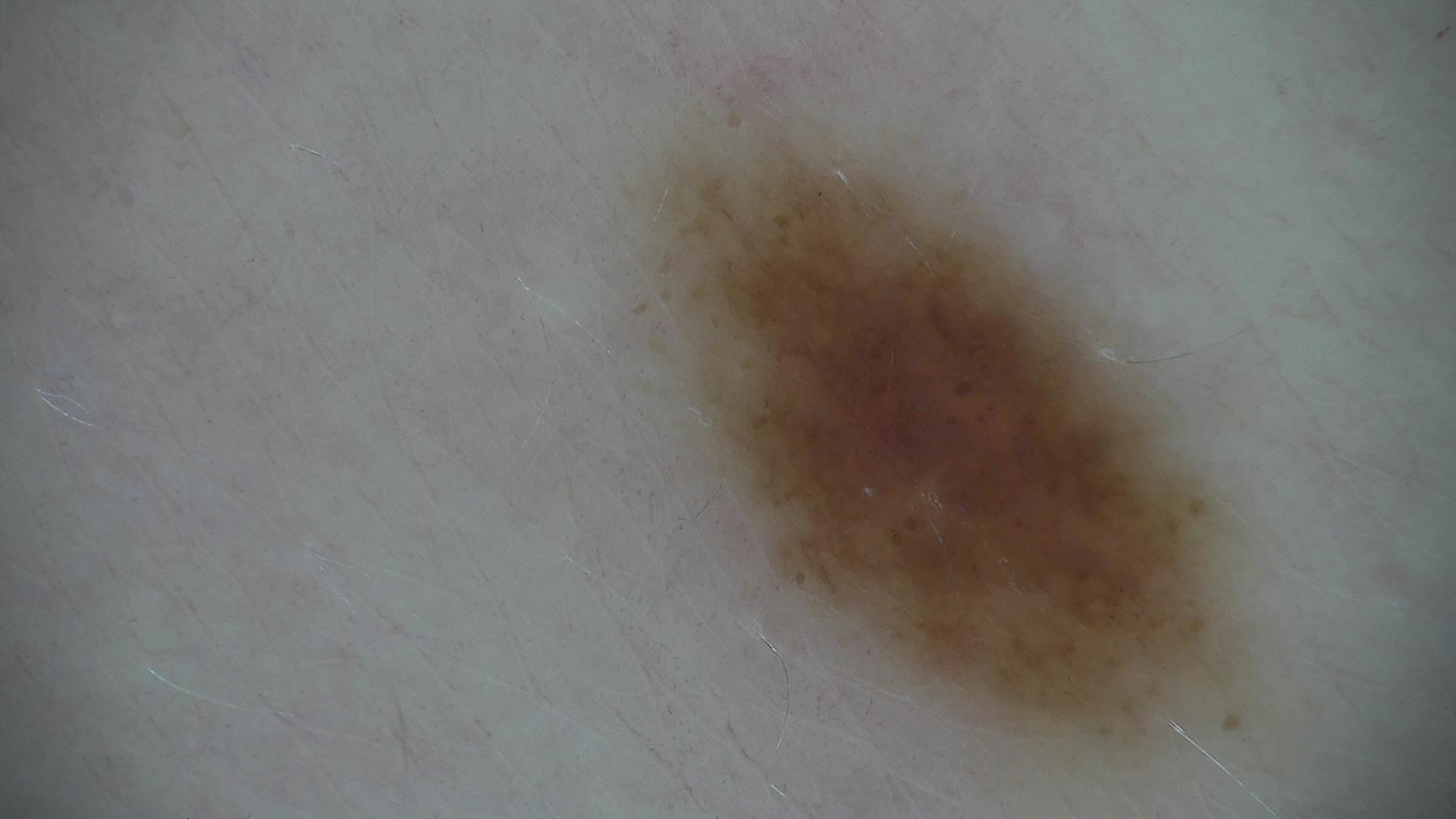Labeled as a dysplastic junctional nevus.